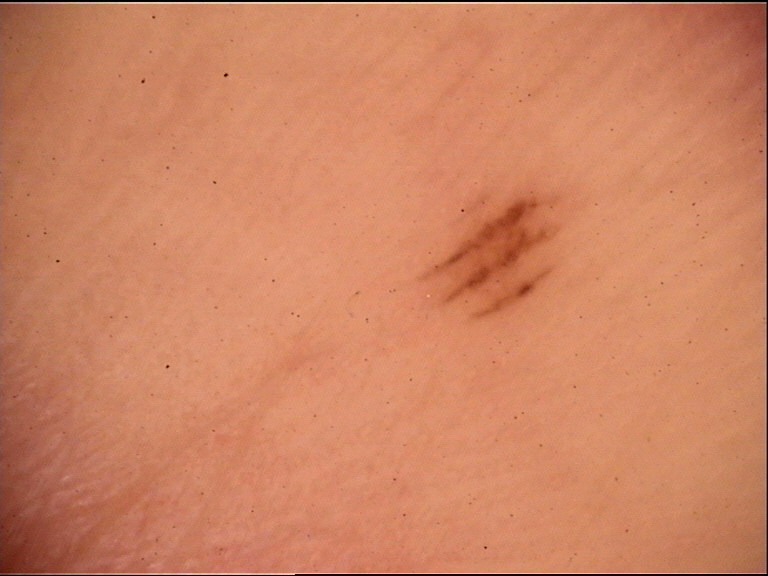Diagnosed as an acral junctional nevus.